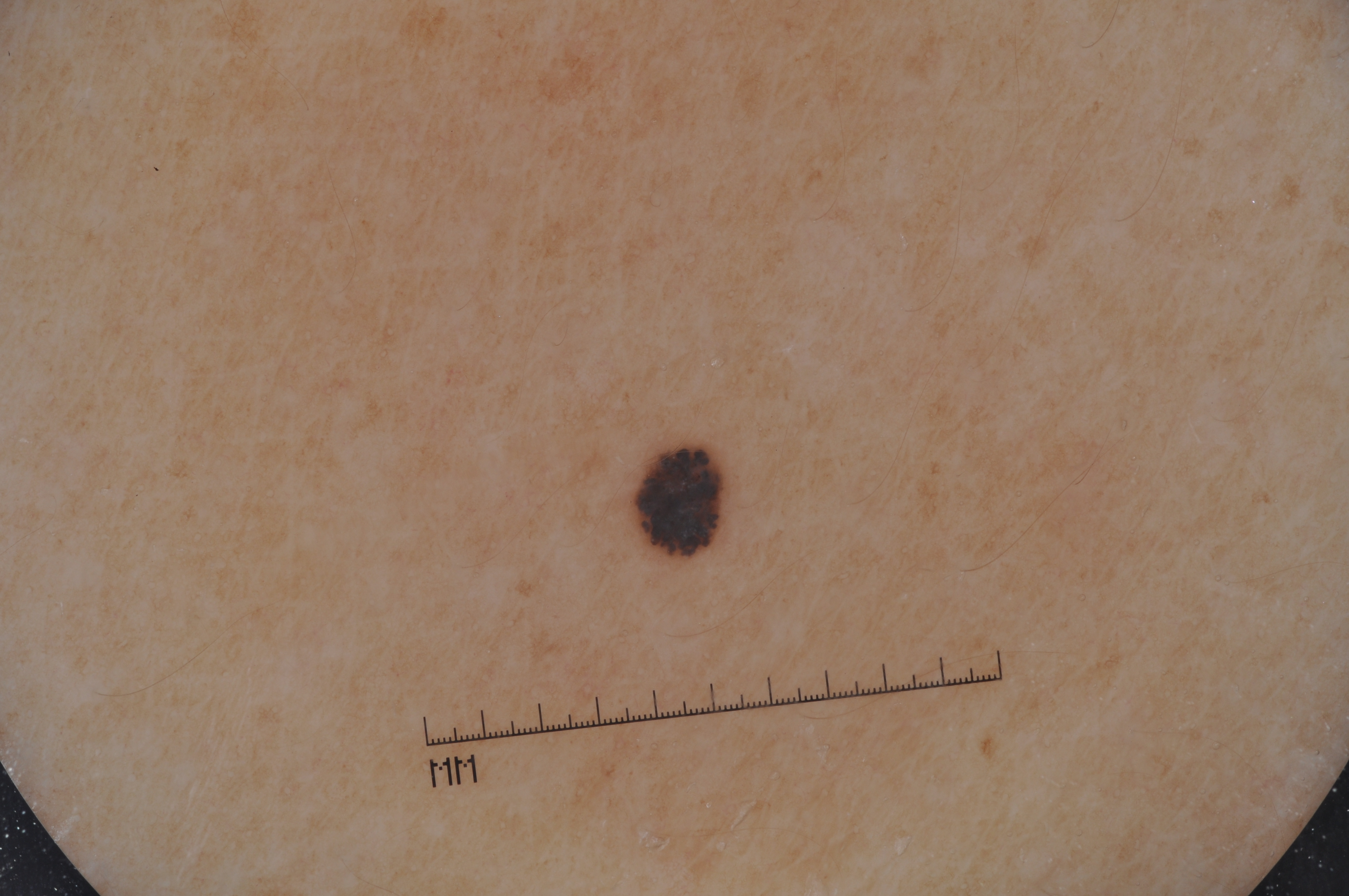A skin lesion imaged with a dermatoscope. The lesion is small relative to the field of view. Dermoscopic examination shows streaks. As (left, top, right, bottom), lesion location: 627 437 733 562. Expert review diagnosed this as a melanocytic nevus.